A skin lesion imaged with a dermatoscope.
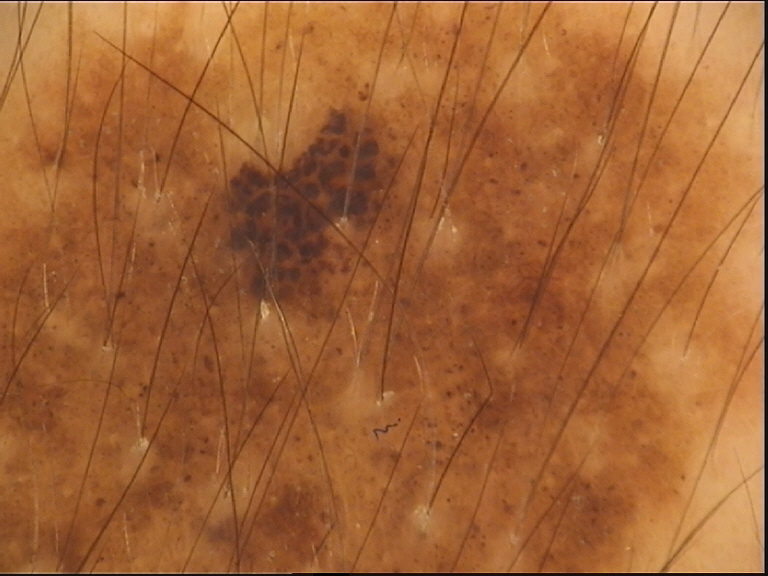Case:
* subtype: banal
* diagnostic label: congenital junctional nevus (expert consensus)